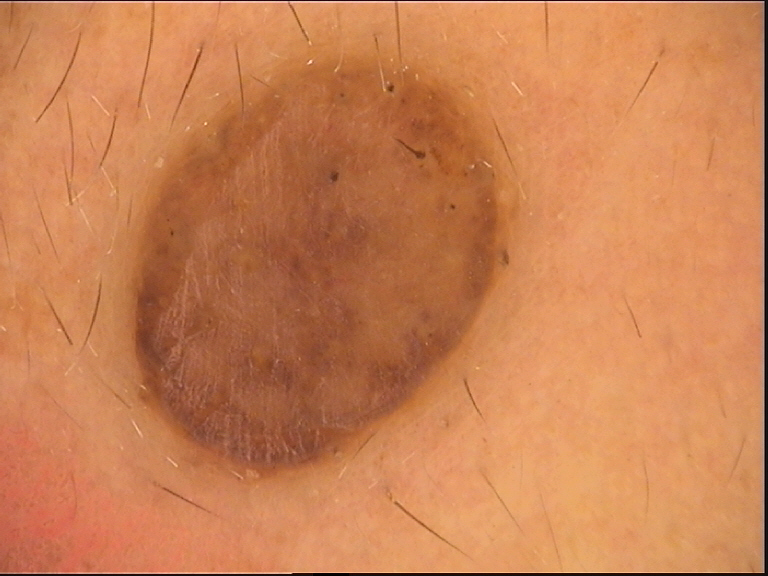The diagnosis was a dermal nevus.